The patient indicates burning and itching. Female subject, age 40–49. The patient indicates the lesion is raised or bumpy and rough or flaky. The affected area is the arm, leg and head or neck. This is a close-up image — 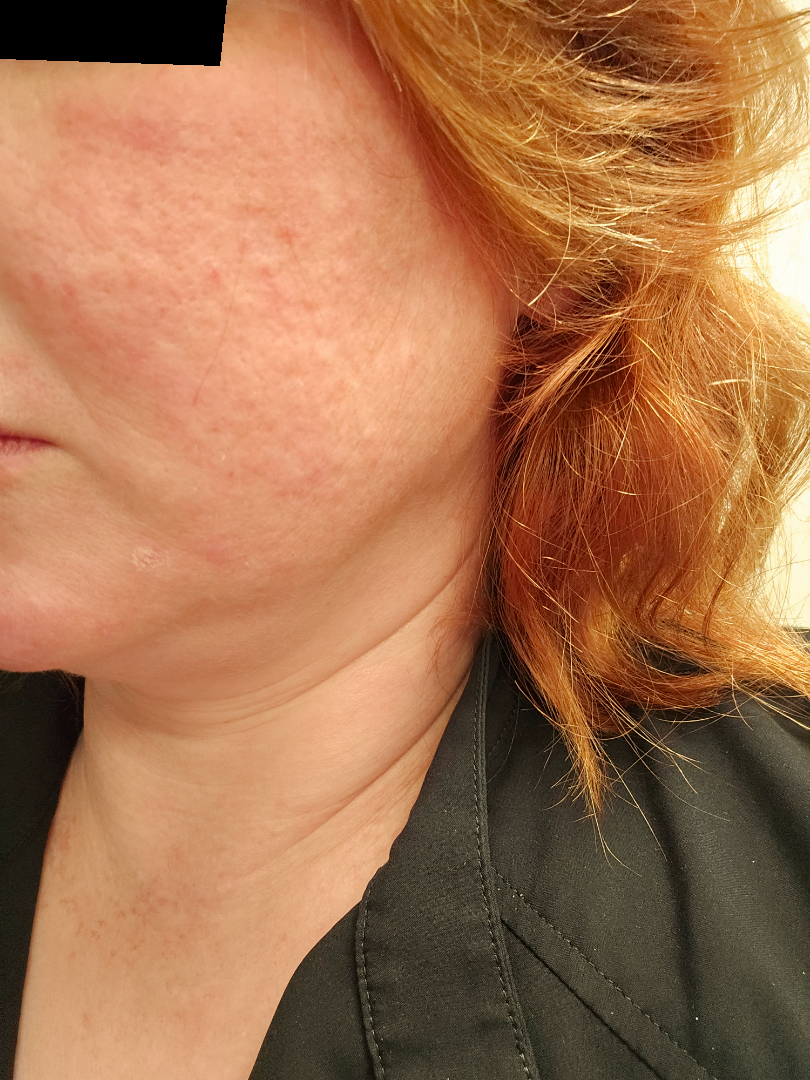Most likely Rosacea; the differential also includes Rosai Dorfman disease.